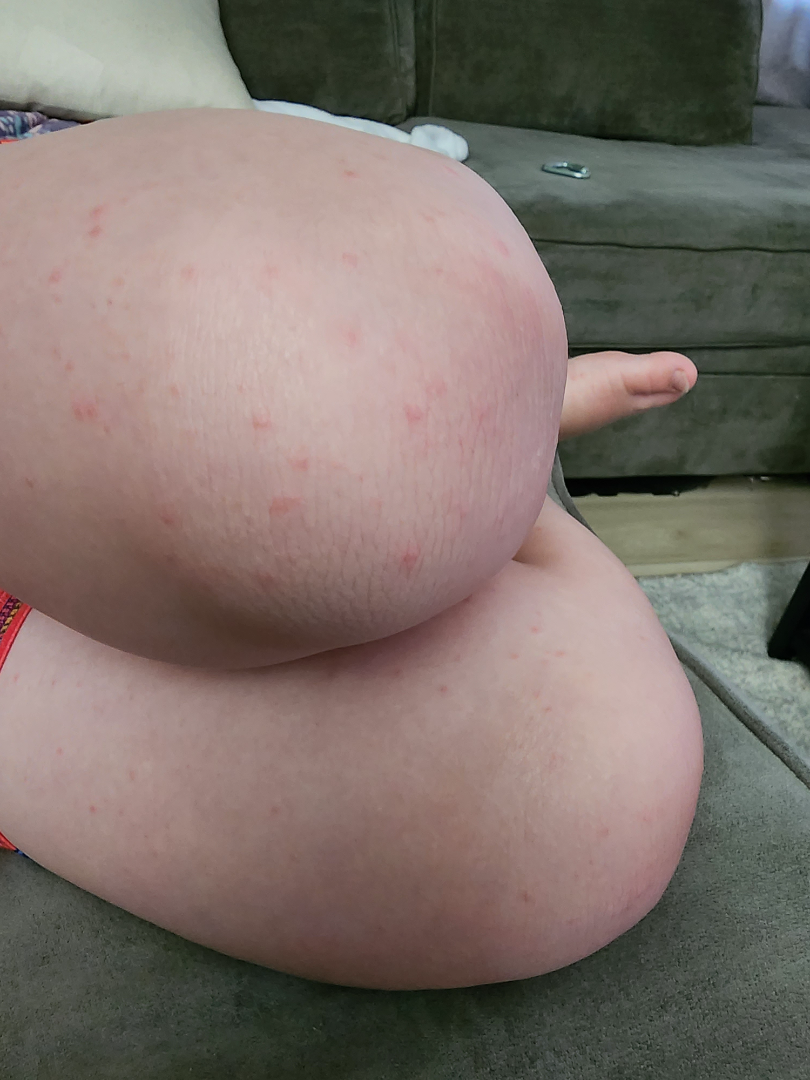Assessment:
The reviewer was unable to grade this case for skin condition.
Clinical context:
The patient considered this a rash. The lesion involves the top or side of the foot and leg. No associated systemic symptoms reported. The patient notes bothersome appearance. The lesion is described as raised or bumpy. Present for about one day. A close-up photograph.